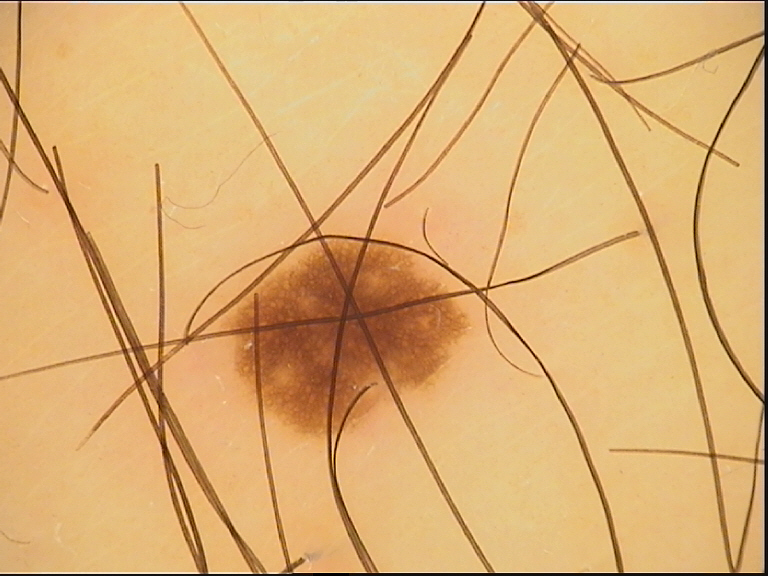image = dermoscopy | diagnosis = junctional nevus (expert consensus).